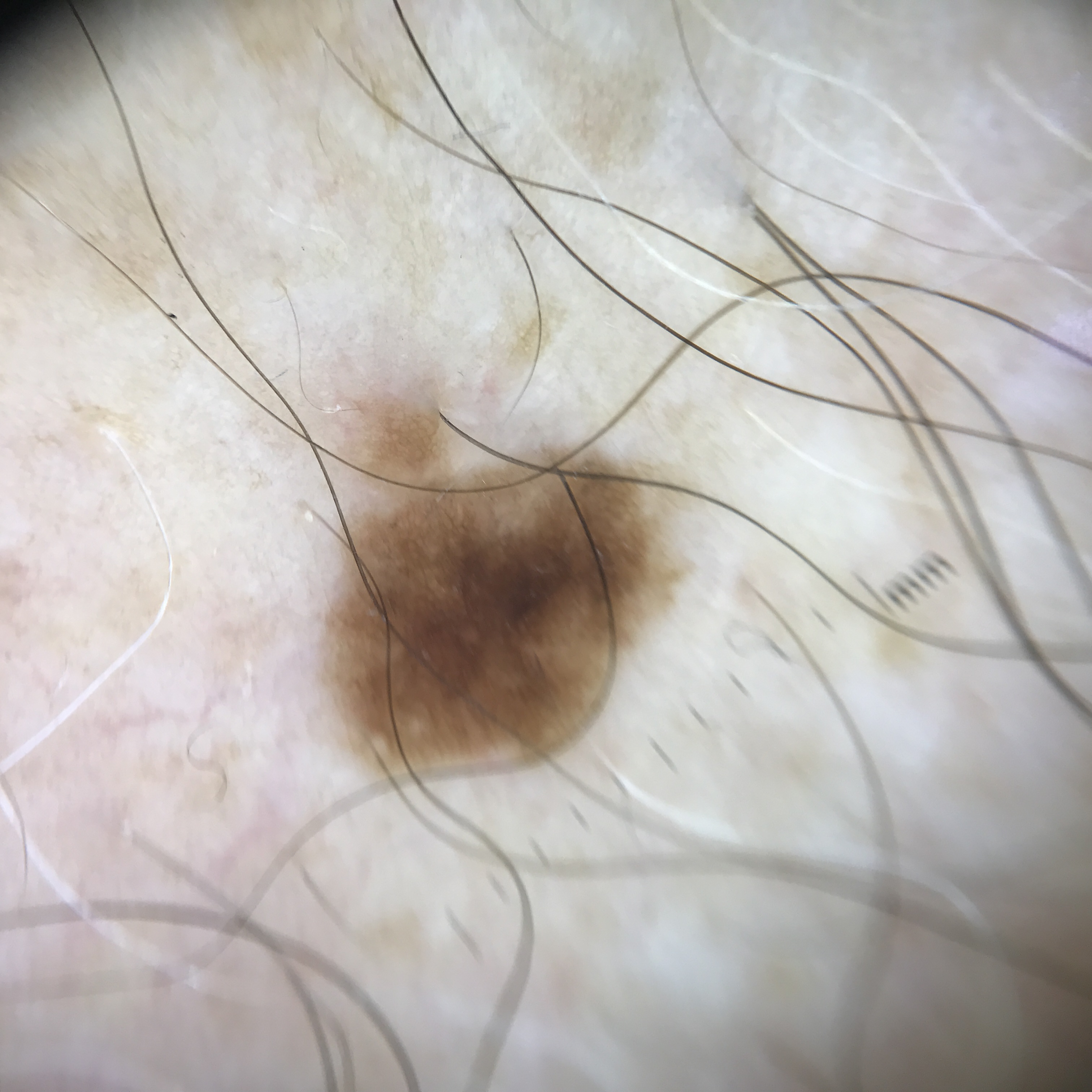<dermoscopy>
<image>dermoscopy</image>
<lesion_type>
<main_class>banal</main_class>
<pattern>junctional</pattern>
</lesion_type>
<diagnosis>
<name>junctional nevus</name>
<code>jb</code>
<malignancy>benign</malignancy>
<super_class>melanocytic</super_class>
<confirmation>expert consensus</confirmation>
</diagnosis>
</dermoscopy>